A dermatoscopic image of a skin lesion.
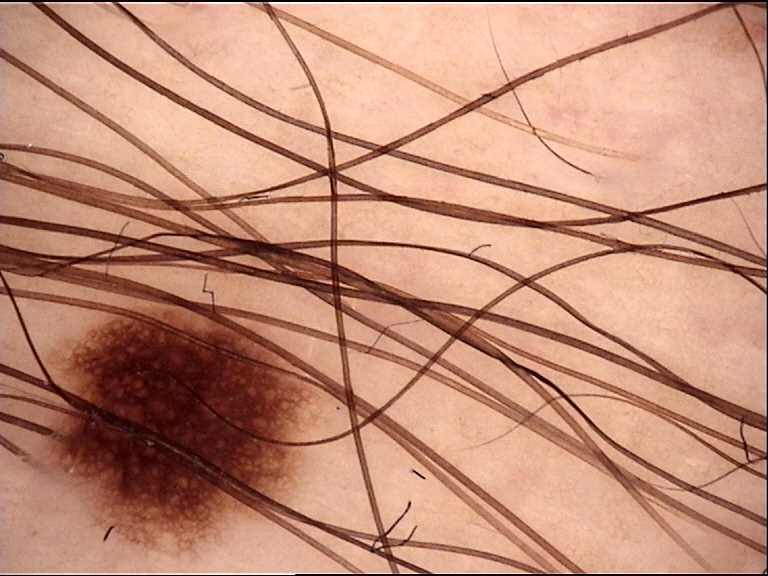<dermoscopy>
<diagnosis>
<name>dysplastic junctional nevus</name>
<code>jd</code>
<malignancy>benign</malignancy>
<super_class>melanocytic</super_class>
<confirmation>expert consensus</confirmation>
</diagnosis>
</dermoscopy>